The patient is male; this image was taken at a distance; the affected area is the leg.
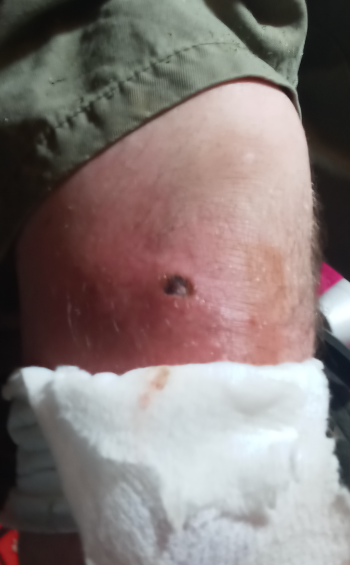impression: the favored diagnosis is Ecthyma; also raised was Abrasion, scrape, or scab; the differential also includes Abscess.